Dermoscopy of a skin lesion.
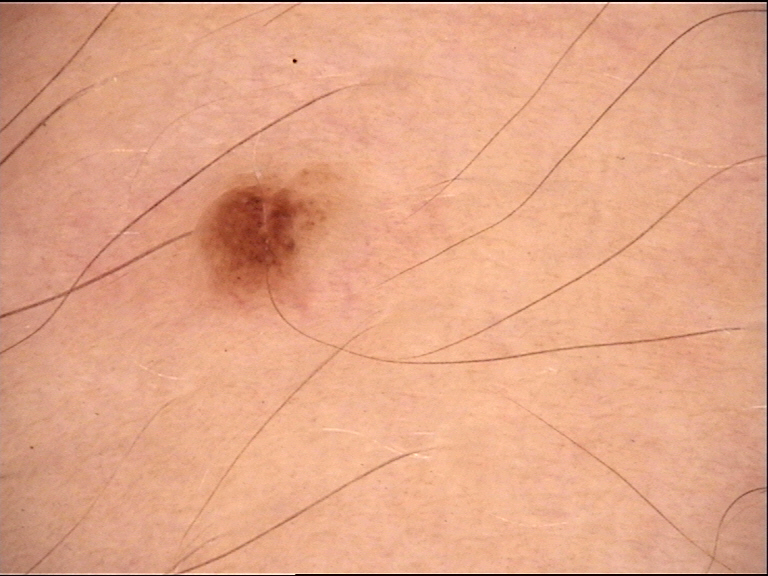assessment = dysplastic compound nevus (expert consensus).